A dermoscopic close-up of a skin lesion — 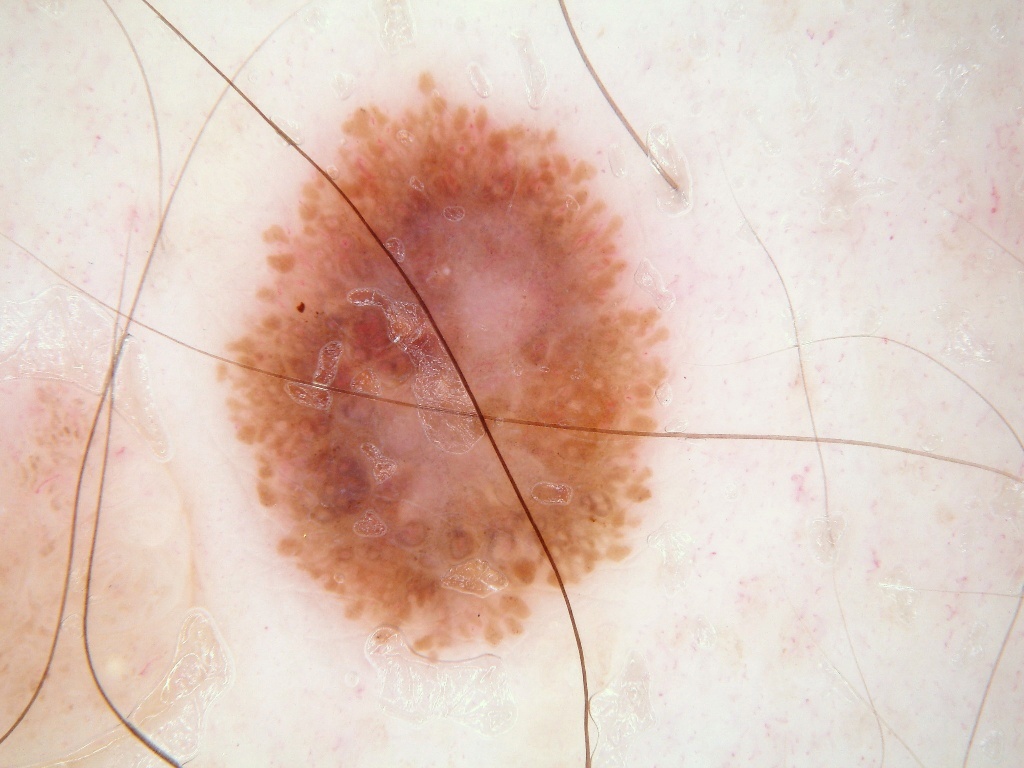extent = ~28% of the field
lesion location = x1=205, y1=60, x2=677, y2=692
diagnosis = a malignant skin lesion